A clinical close-up photograph of a skin lesion · a subject in their 70s:
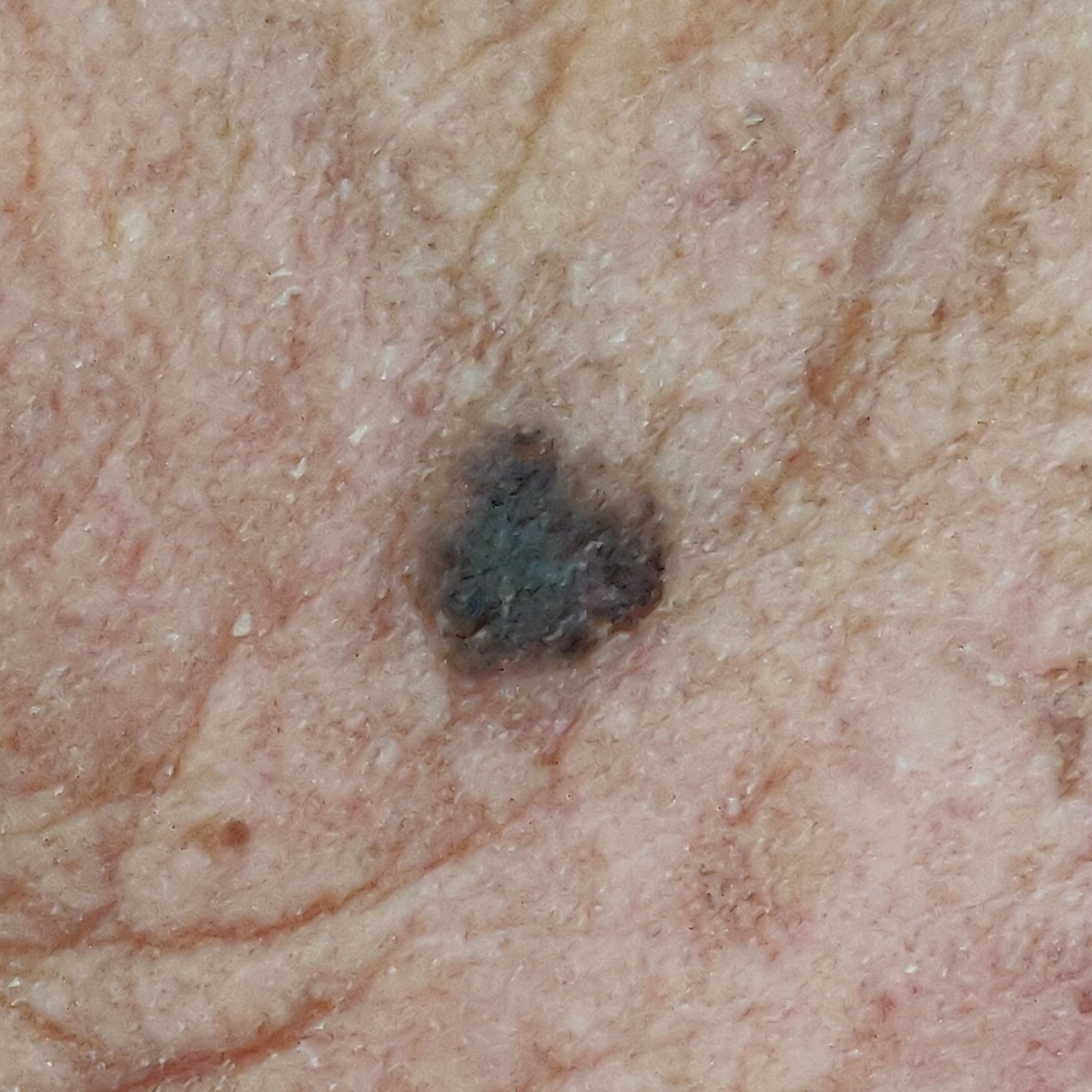{
  "lesion_location": "the face",
  "symptoms": {
    "present": [
      "itching",
      "elevation",
      "growth"
    ],
    "absent": [
      "change in appearance",
      "pain"
    ]
  },
  "diagnosis": {
    "name": "seborrheic keratosis",
    "code": "SEK",
    "malignancy": "benign",
    "confirmation": "clinical consensus"
  }
}